Present for less than one week; texture is reported as flat; this is a close-up image; the contributor is 18–29, male; the leg is involved:
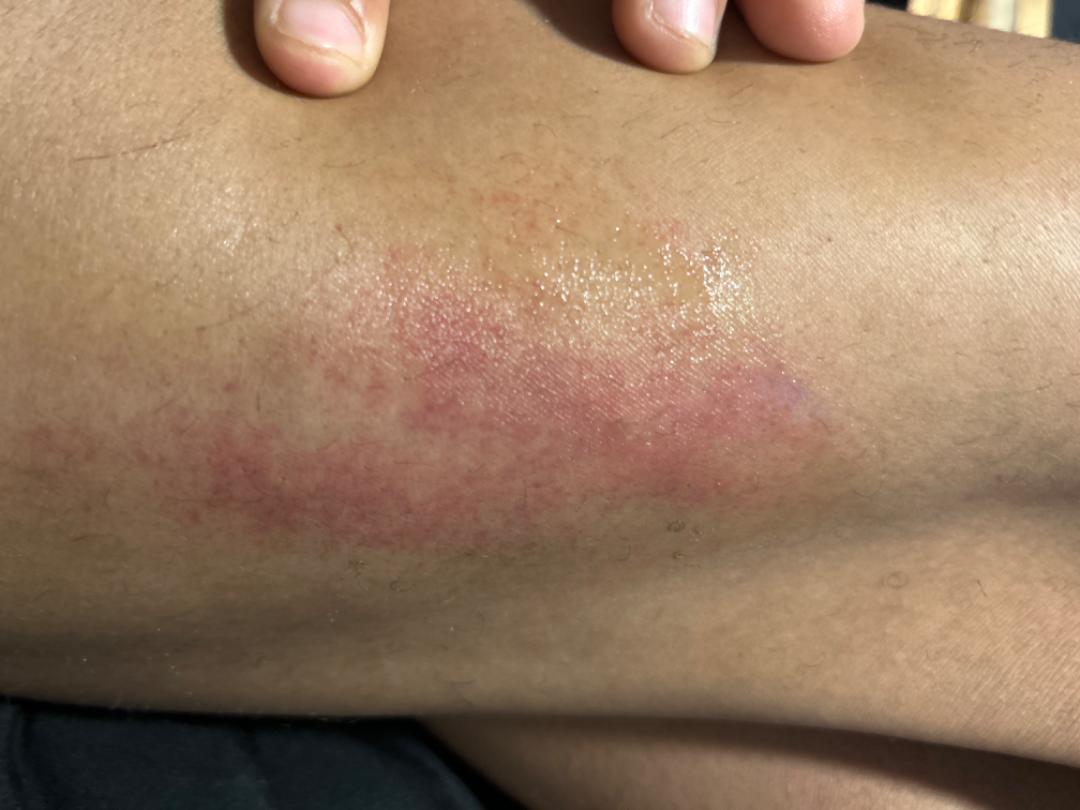differential=the impression was split between Insect Bite; ecchymoses; and Acute dermatitis, NOS; a more distant consideration is Irritant Contact Dermatitis.